The leg is involved · the photo was captured at a distance · the patient is a male aged 40–49 — 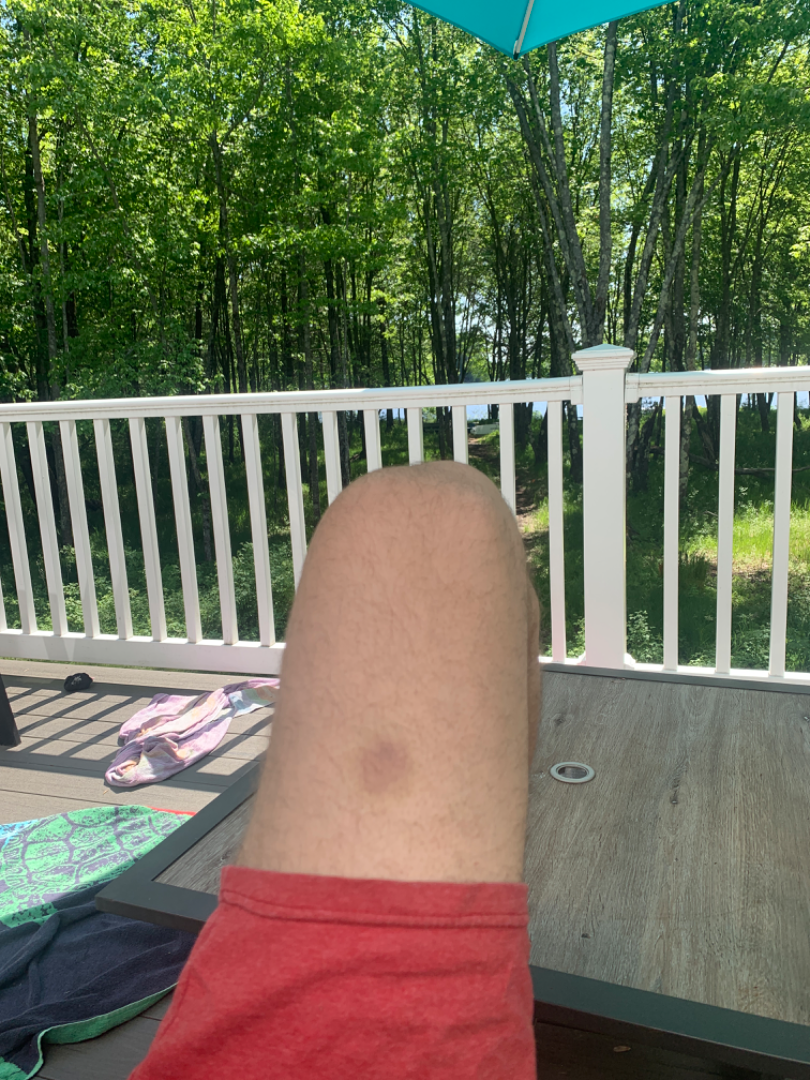On photographic review by a dermatologist: most likely Drug Rash; an alternative is ecchymoses.